A dermoscopic photograph of a skin lesion.
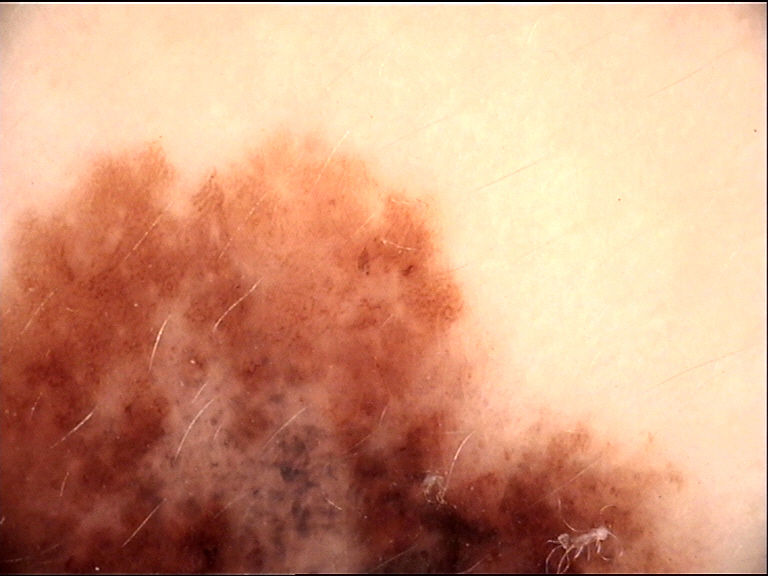Q: What is this lesion?
A: melanoma (biopsy-proven)